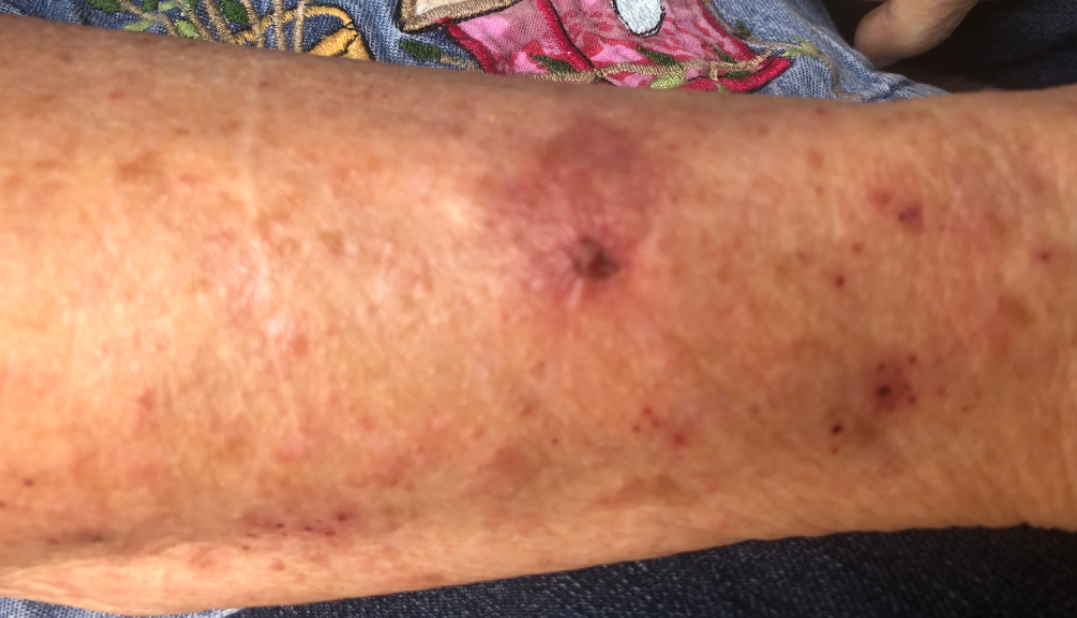Close-up view.